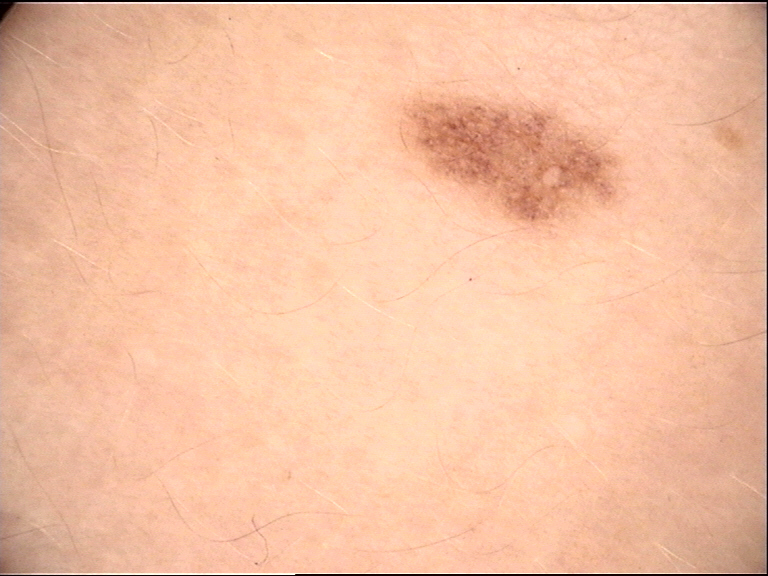modality: dermoscopy; class: dysplastic junctional nevus (expert consensus).